The chart records prior malignancy (patient or family). A clinical photo of a skin lesion taken with a smartphone. A female subject in their 60s. The patient is Fitzpatrick phototype III.
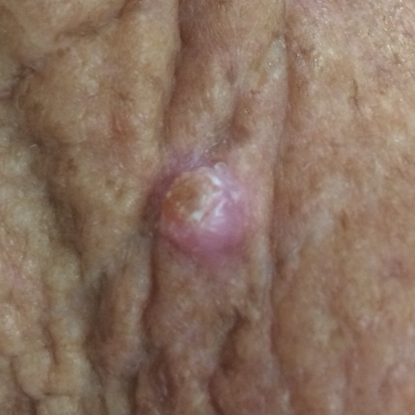The lesion is located on the neck. The lesion measures 5 × 4 mm. By the patient's account, the lesion is elevated and itches, but does not hurt. Biopsy-confirmed as a squamous cell carcinoma.